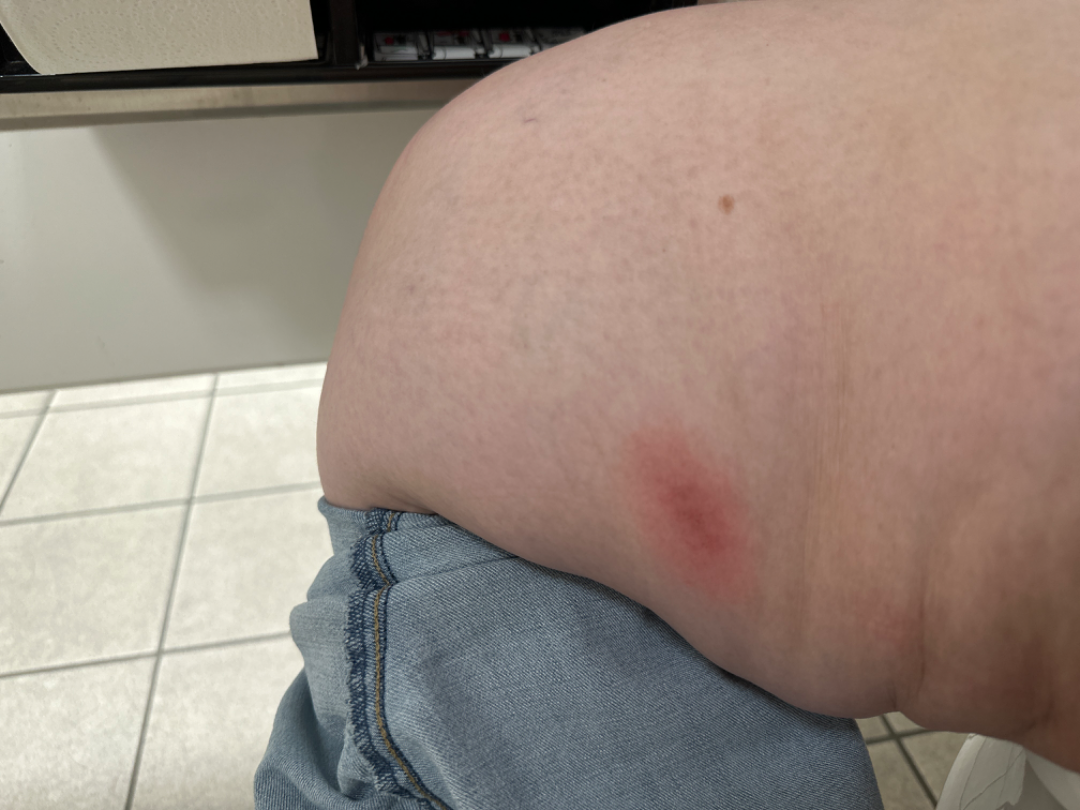The photo was captured at a distance.
The leg is involved.
Female subject, age 18–29.
On remote dermatologist review: most consistent with Eczema; also consider Geographic tongue.